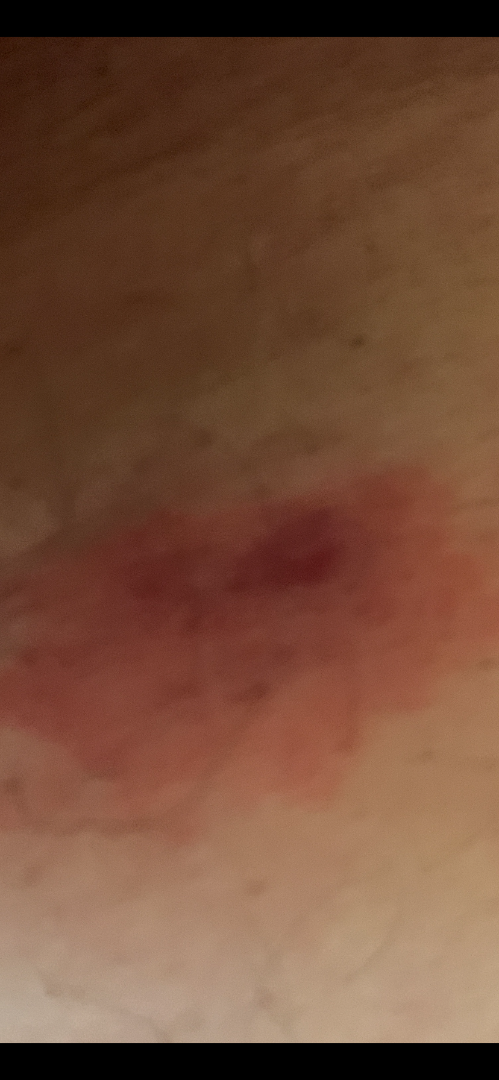assessment — unable to determine; image framing — close-up.